Dermoscopy of a skin lesion.
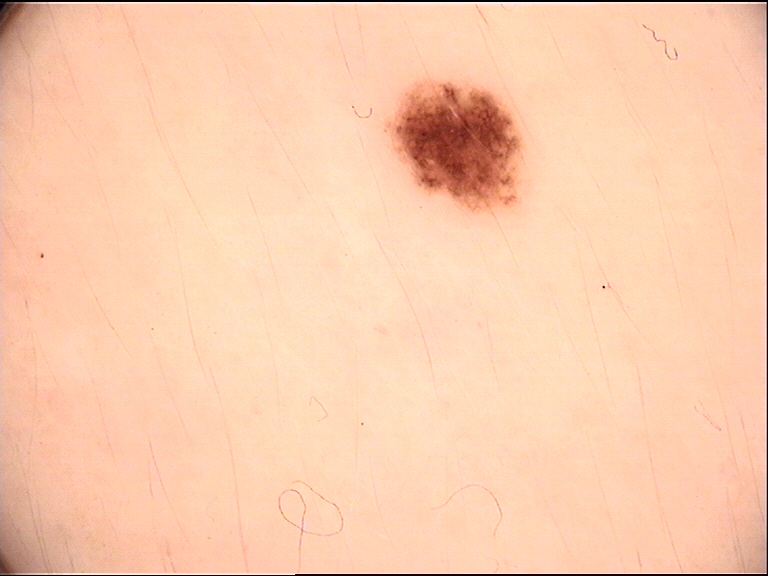Q: What is the diagnosis?
A: dysplastic junctional nevus (expert consensus)